The chart notes prior skin cancer (patient or family); a female subject 36 years of age; a clinical photograph showing a skin lesion.
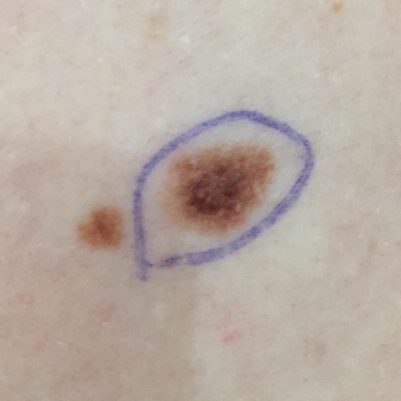The lesion measures approximately 8 × 6 mm.
The patient reports that the lesion has grown, but has not bled.
The biopsy diagnosis was a benign skin lesion — a nevus.